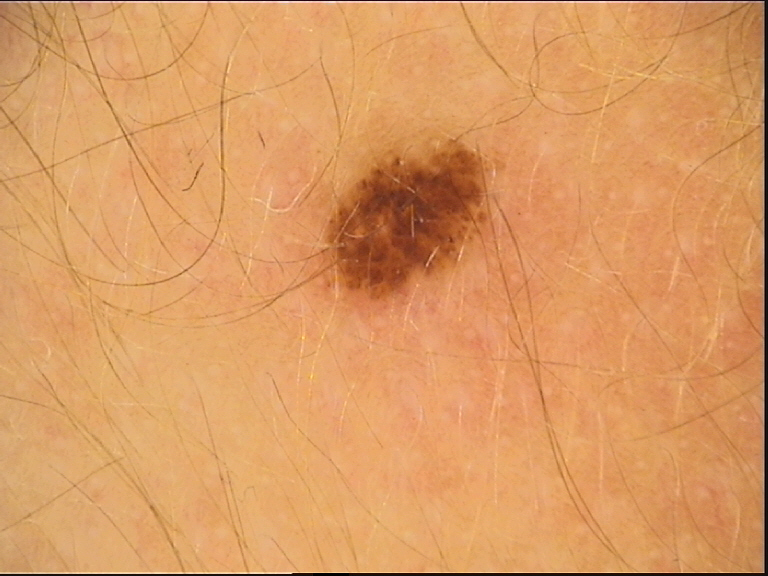class: dysplastic junctional nevus (expert consensus).